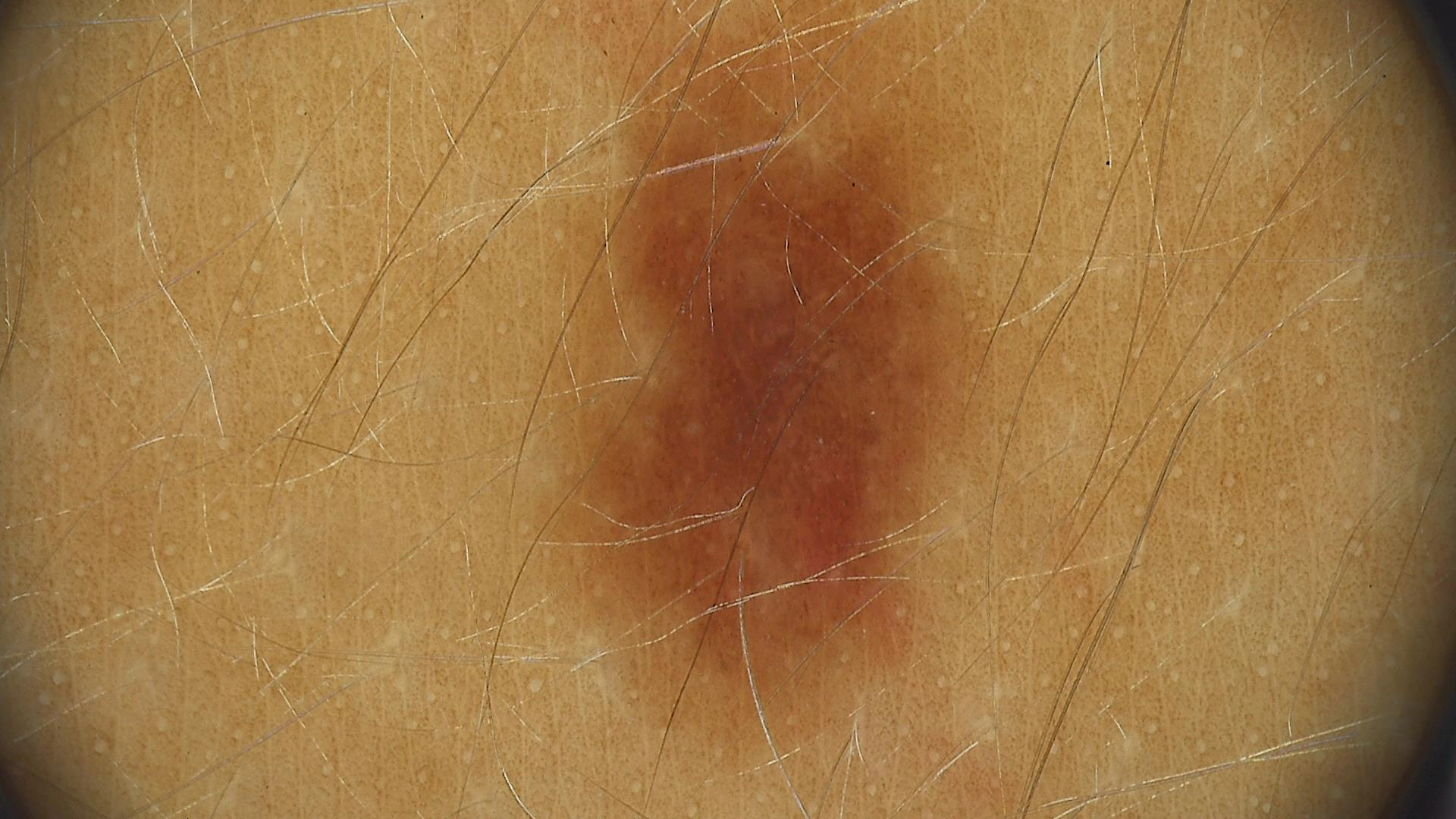• assessment: dysplastic junctional nevus (expert consensus)